Collected as part of a research study, without a referral diagnosis · the patient says their skin reddens with sun exposure · on a questionnaire the patient reported a history of sunbed use · a macroscopic clinical photograph of a skin lesion:
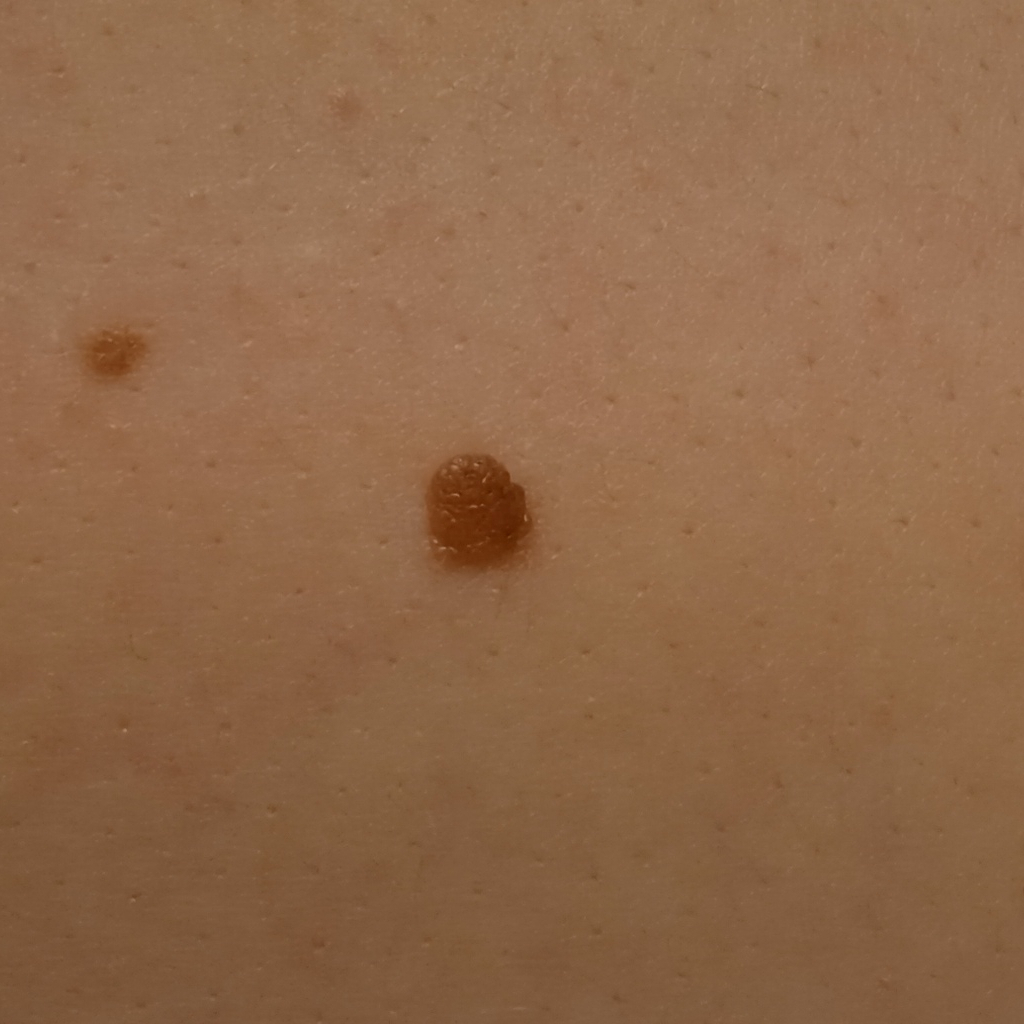Findings:
Located on the back. The lesion is about 5.5 mm across.
Impression:
The consensus diagnosis for this lesion was a melanocytic nevus.